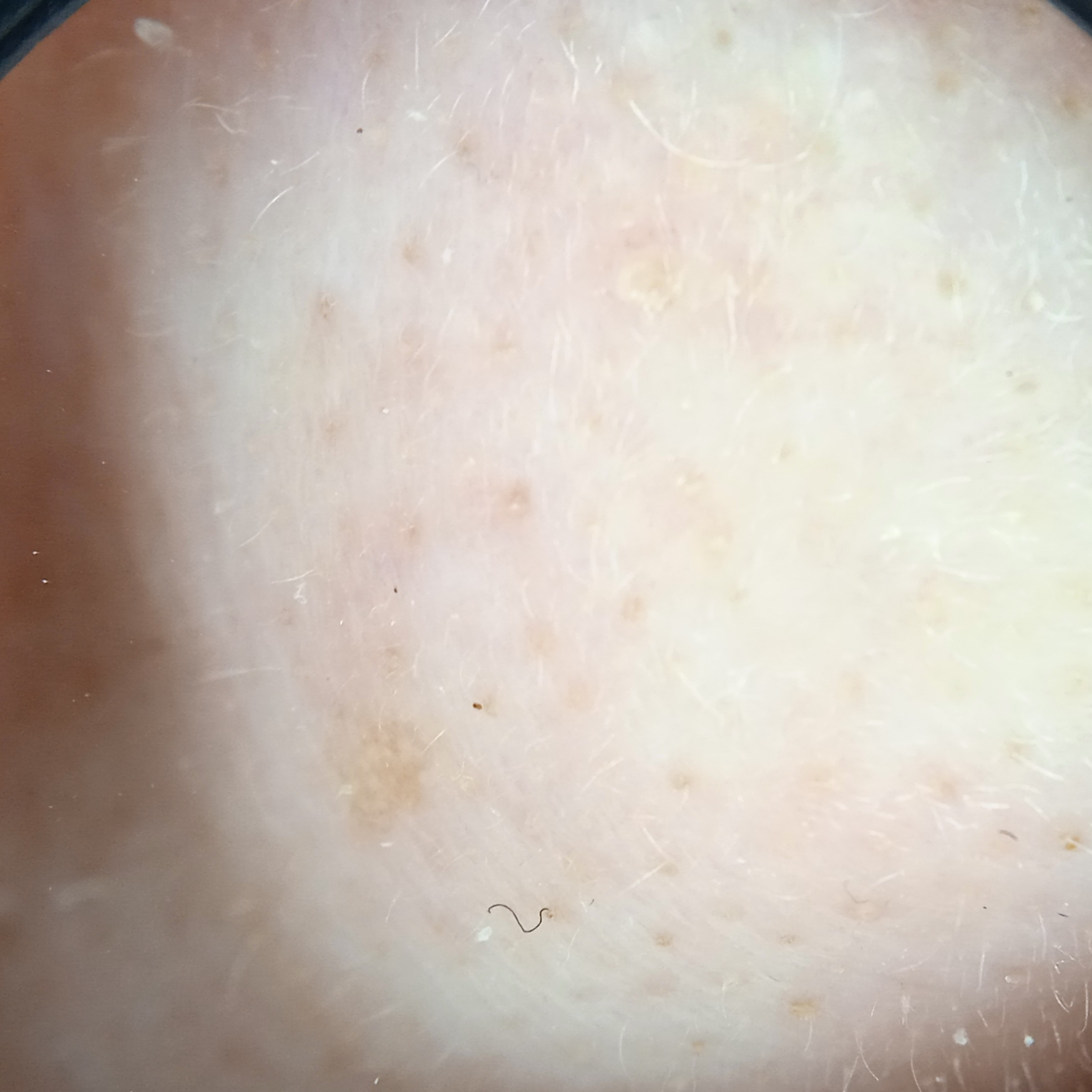<skin_lesion>
  <diagnosis>
    <name>actinic keratosis</name>
    <malignancy>benign</malignancy>
  </diagnosis>
</skin_lesion>